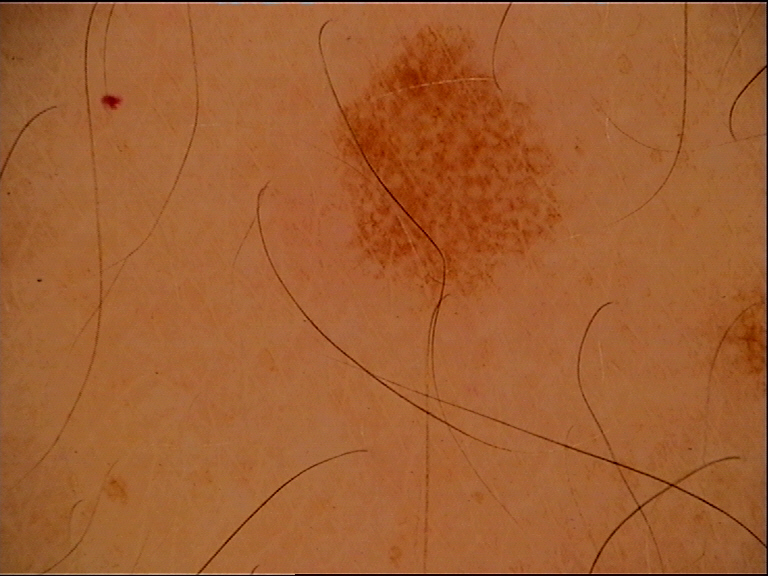assessment: dysplastic junctional nevus (expert consensus)